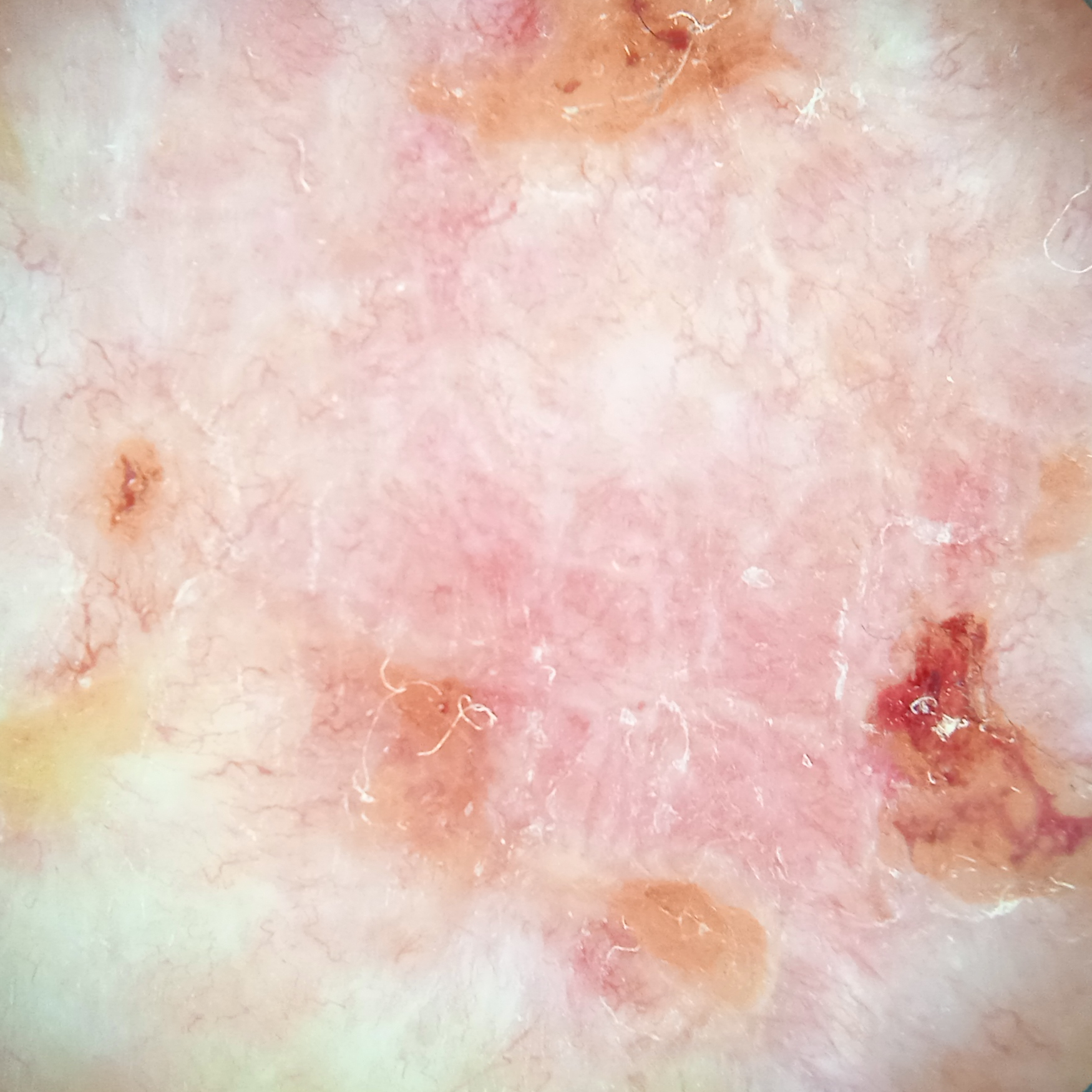A dermatoscopic image of a skin lesion.
A male patient 81 years of age.
The patient says their skin reddens with sun exposure.
Referred for assessment of suspected basal cell carcinoma.
The patient describes having few moles overall.
Located on the back.
The biopsy diagnosis was a basal cell carcinoma, following excision, with a measured thickness of 3 mm.